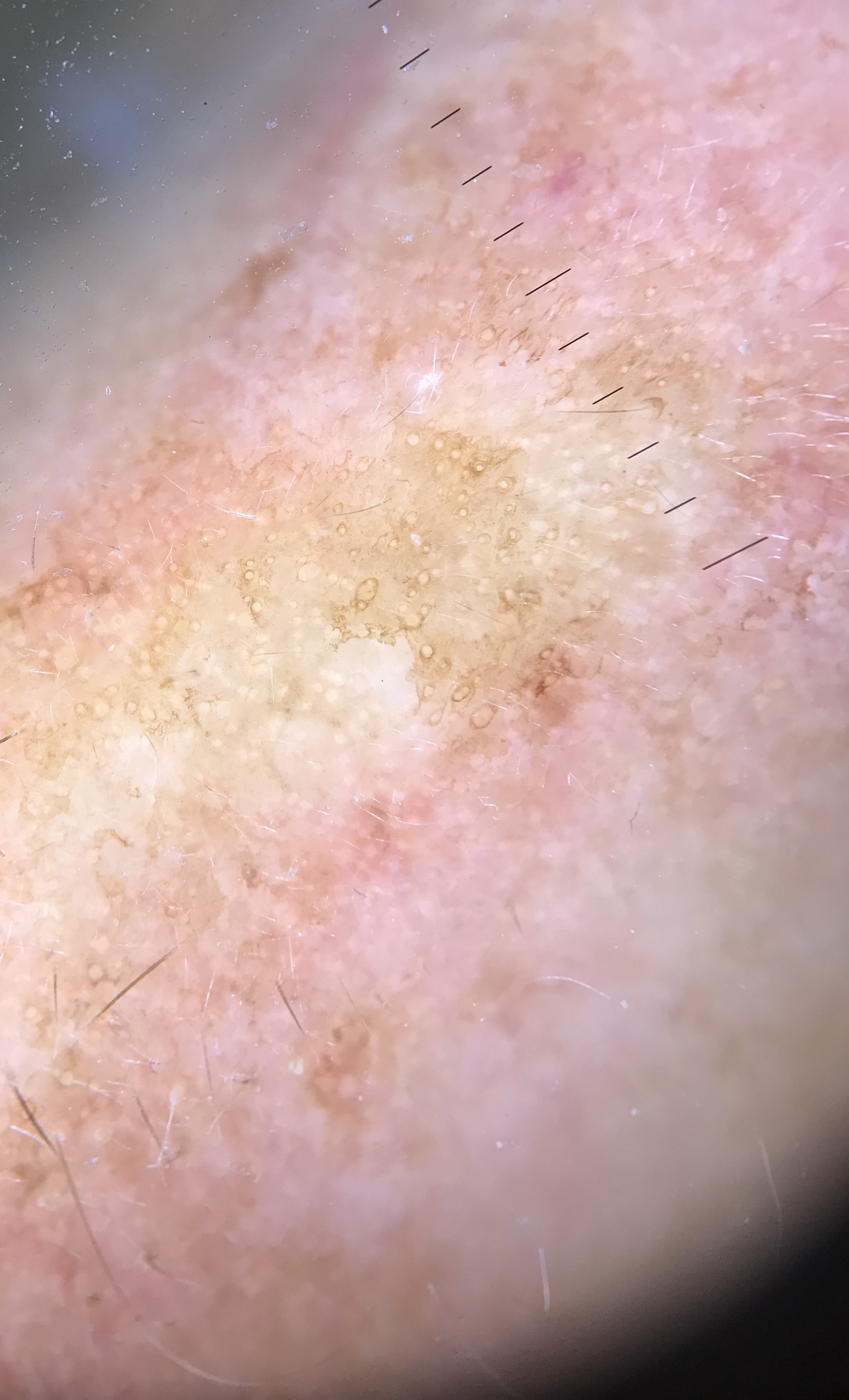Labeled as an actinic keratosis.